Dermoscopy of a skin lesion:
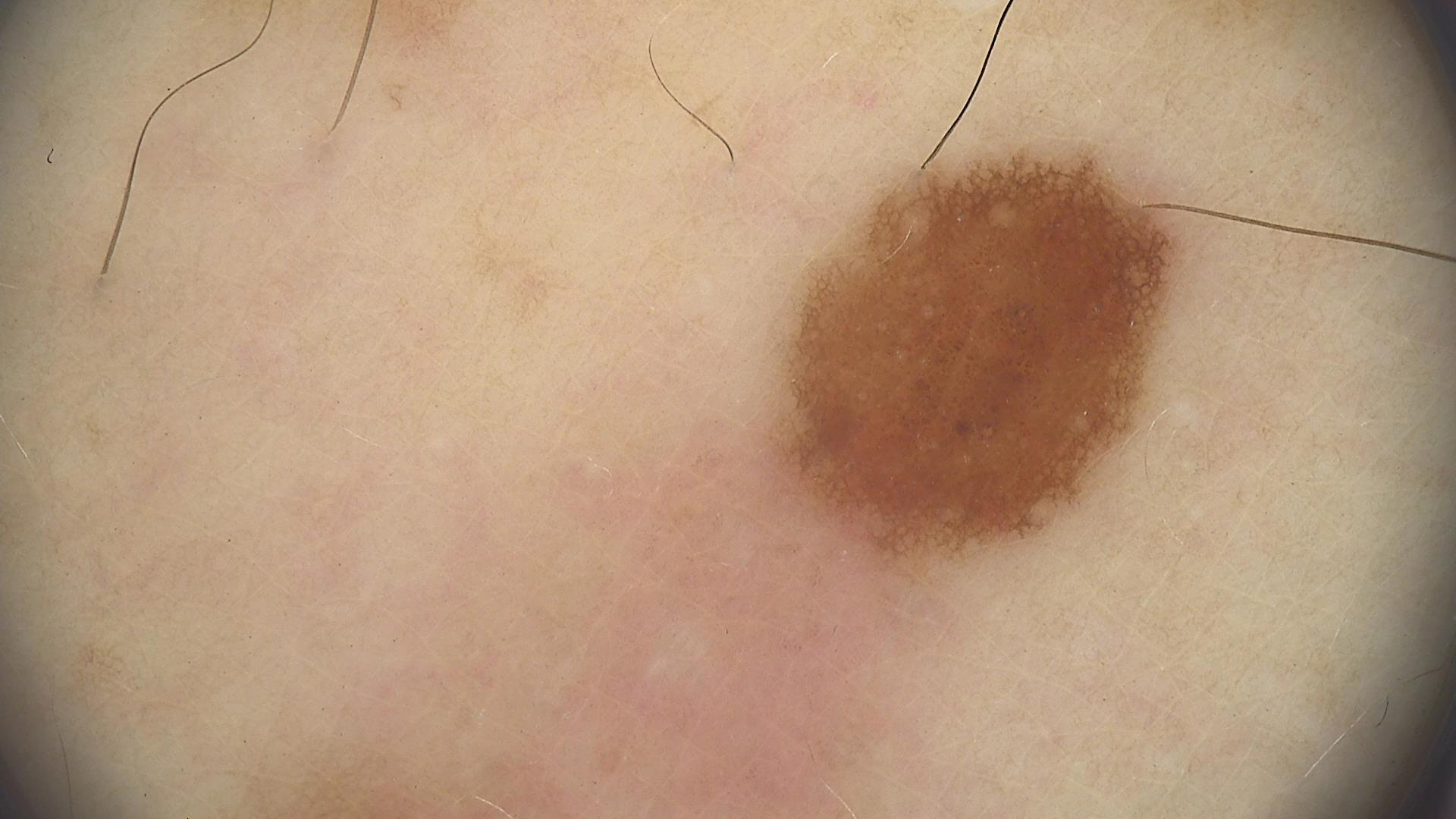diagnostic label = dysplastic junctional nevus (expert consensus).